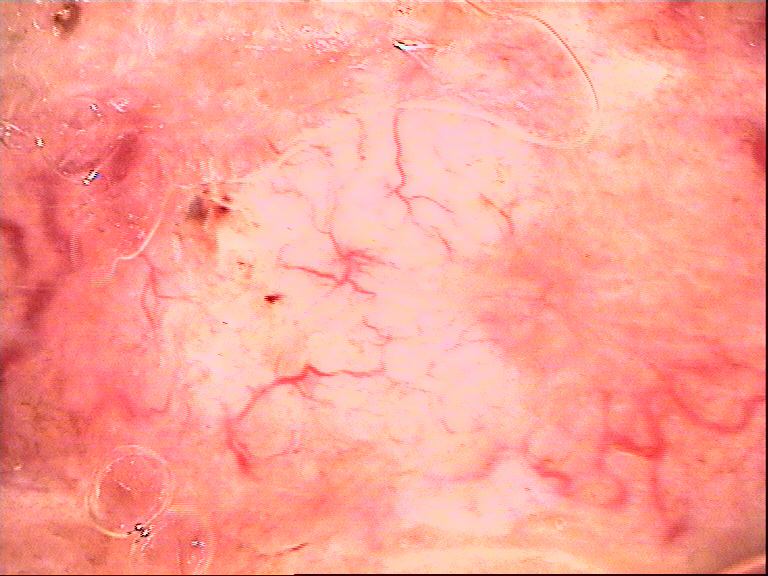Findings:
* label · basal cell carcinoma (biopsy-proven)